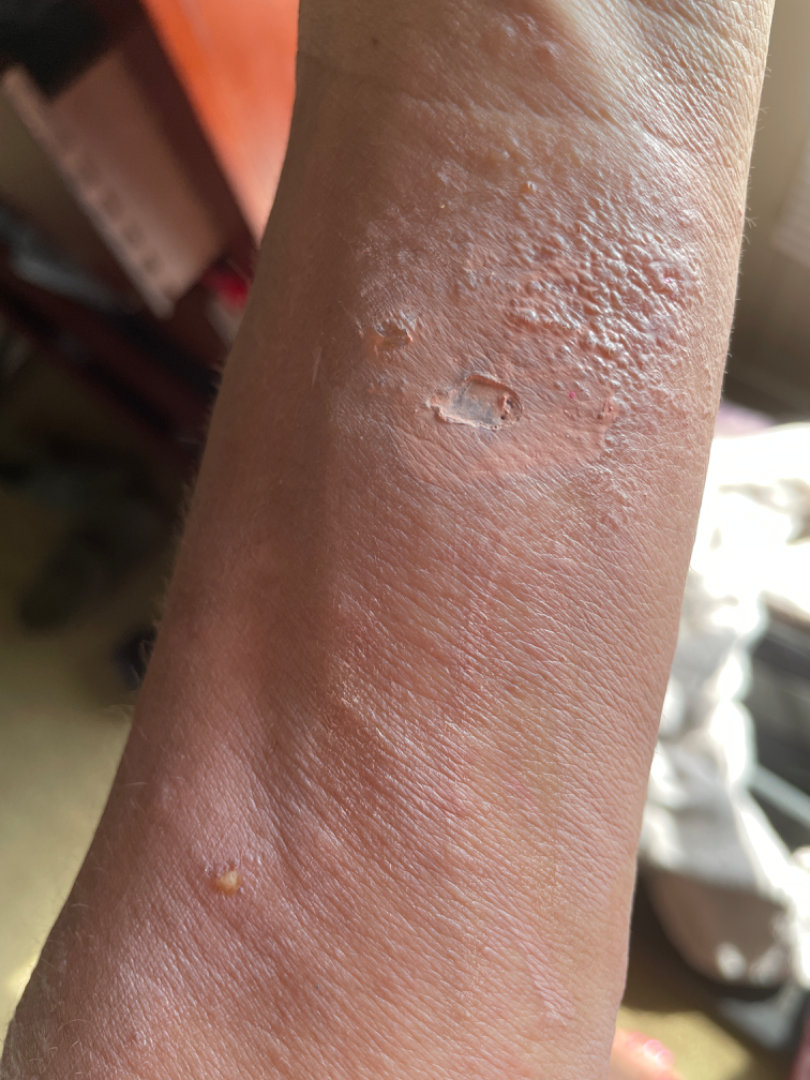skin tone — Fitzpatrick phototype V | location — arm, back of the hand and head or neck | shot type — at an angle | impression — one reviewing dermatologist: most consistent with Allergic Contact Dermatitis; also consider Irritant Contact Dermatitis.